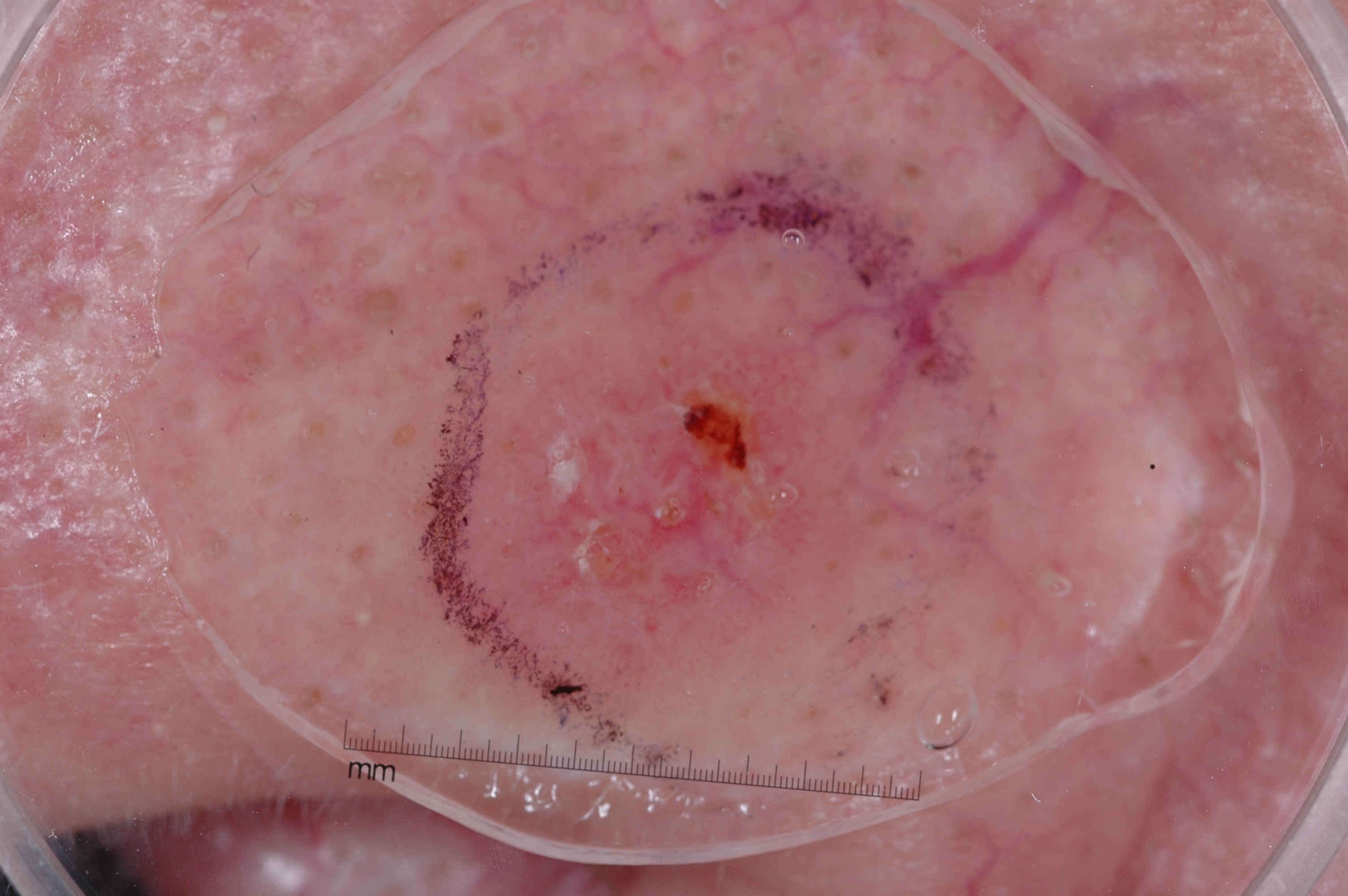Summary: A dermatoscopic image of a skin lesion. A male subject, roughly 50 years of age. Dermoscopic review identifies no negative network, milia-like cysts, streaks, or pigment network. In (x1, y1, x2, y2) order, the lesion spans [469, 275, 896, 689]. A mid-sized lesion within the field. Impression: Expert review diagnosed this as a seborrheic keratosis, a benign skin lesion.